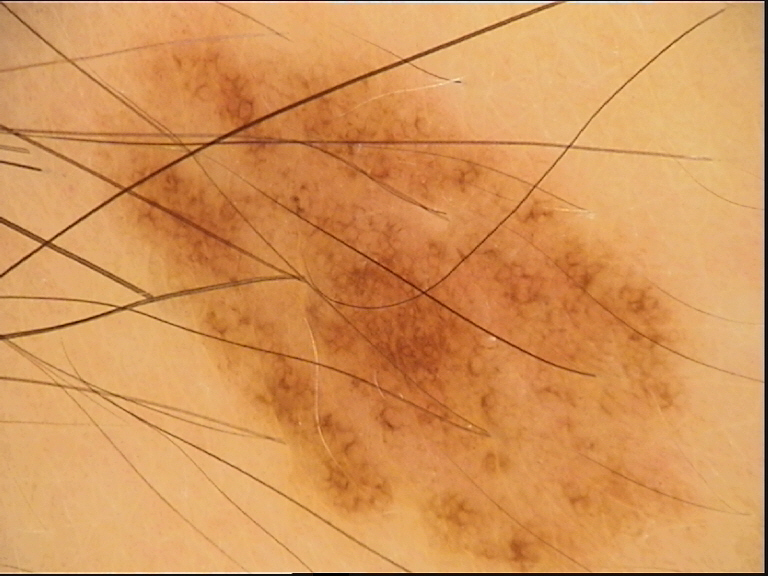Impression: Classified as a dysplastic junctional nevus.